A close-up photograph. Located on the back of the hand.
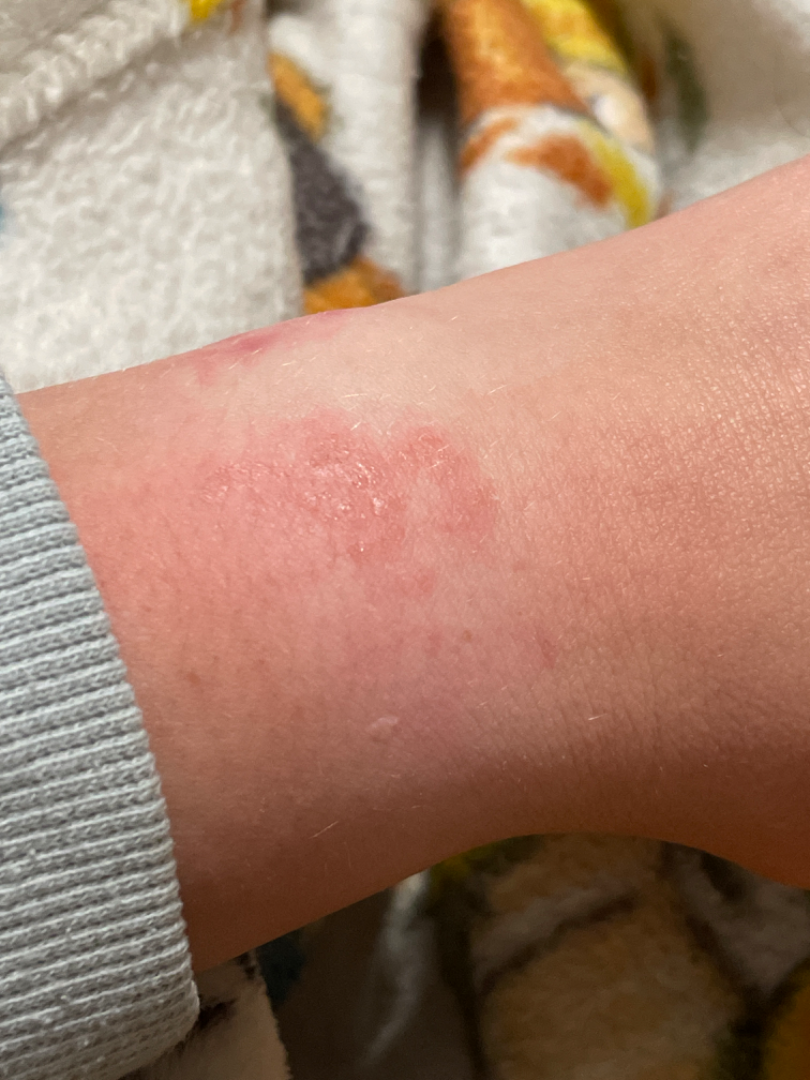Q: Texture?
A: raised or bumpy
Q: Duration?
A: less than one week
Q: Patient's own categorization?
A: a rash
Q: What conditions are considered?
A: in keeping with Allergic Contact Dermatitis